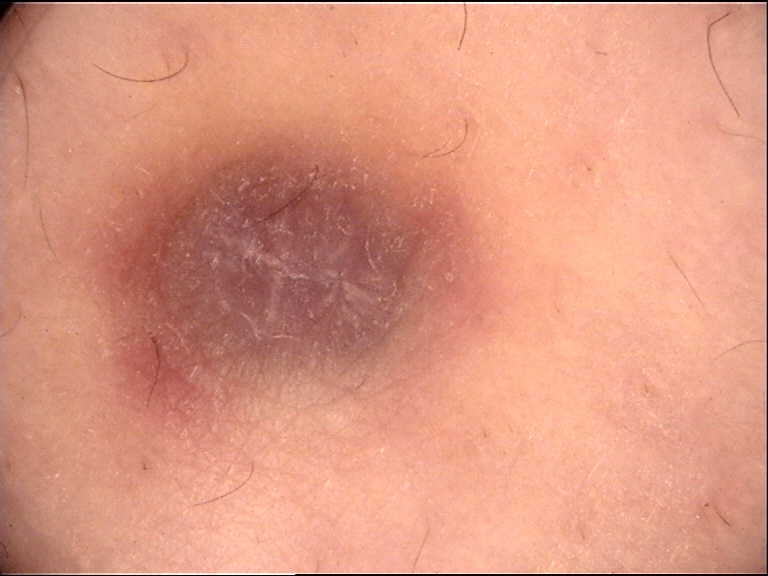– diagnostic label — dermatofibroma (expert consensus)